A dermoscopic photograph of a skin lesion.
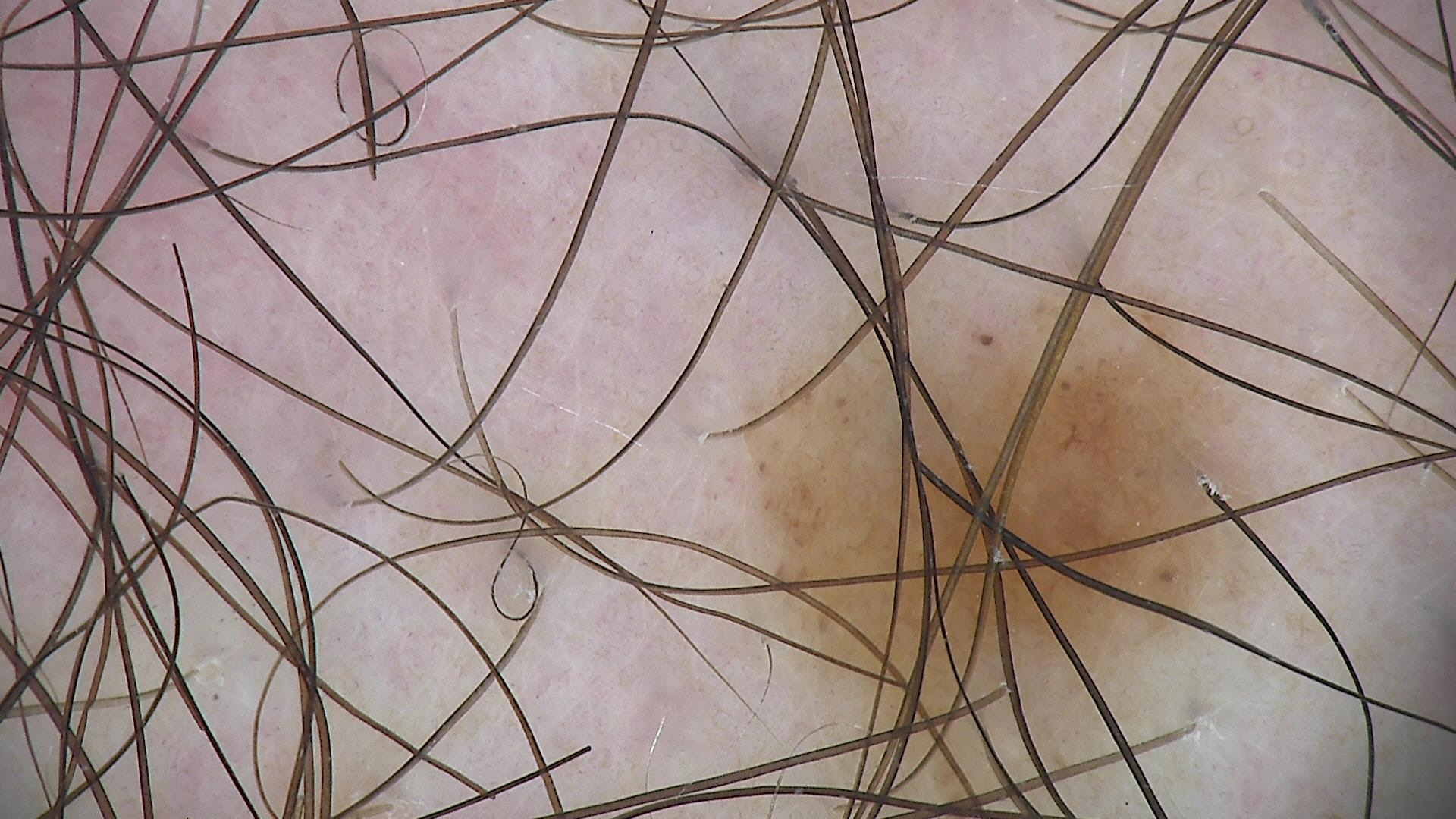Conclusion: Labeled as a dysplastic junctional nevus.